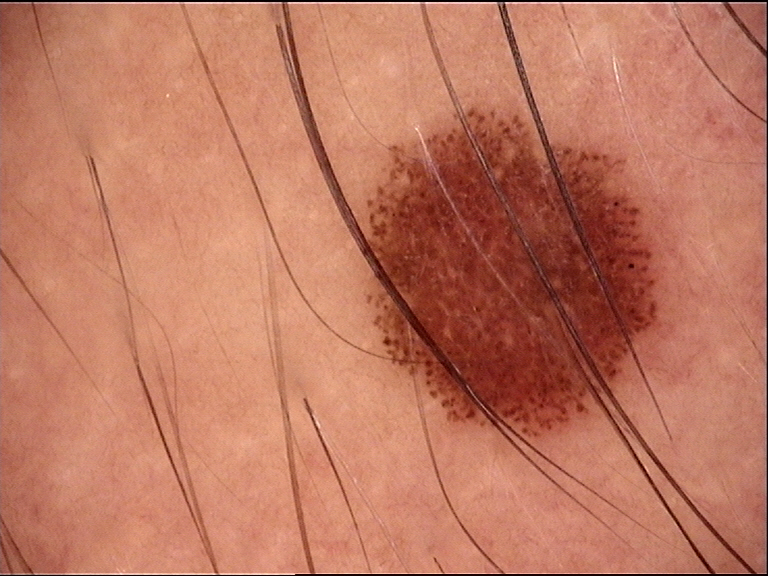Consistent with a dysplastic junctional nevus.